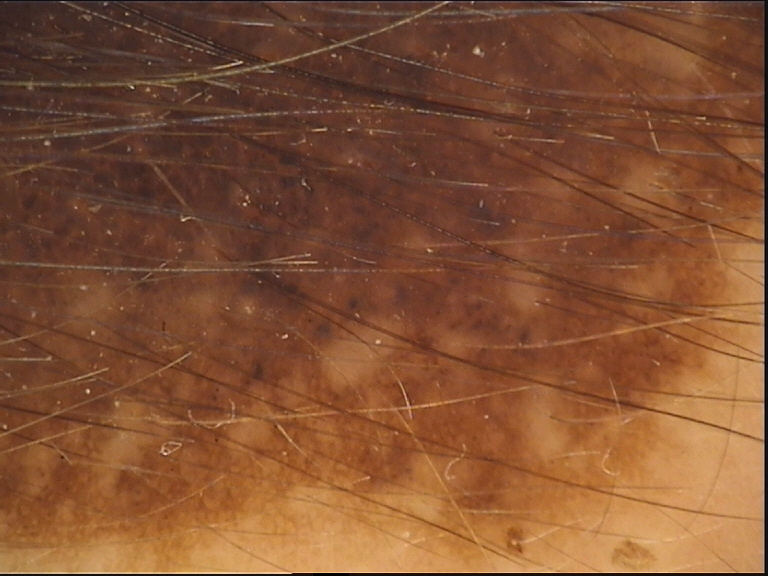<case>
<diagnosis>
<name>congenital compound nevus</name>
<code>ccb</code>
<malignancy>benign</malignancy>
<super_class>melanocytic</super_class>
<confirmation>expert consensus</confirmation>
</diagnosis>
</case>